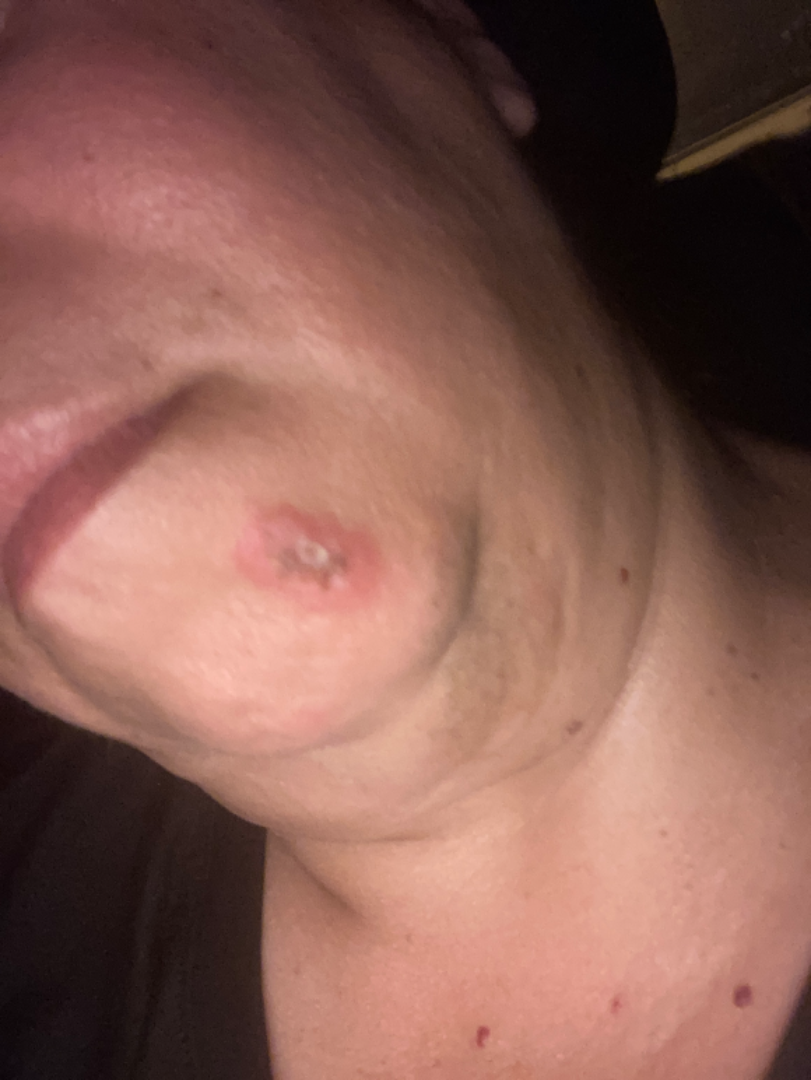impression = the differential, in no particular order, includes Abscess, skin cyst and Odontogenic keratocyst.